Dermoscopy of a skin lesion · imaged for a research study, with no referral diagnosis recorded — 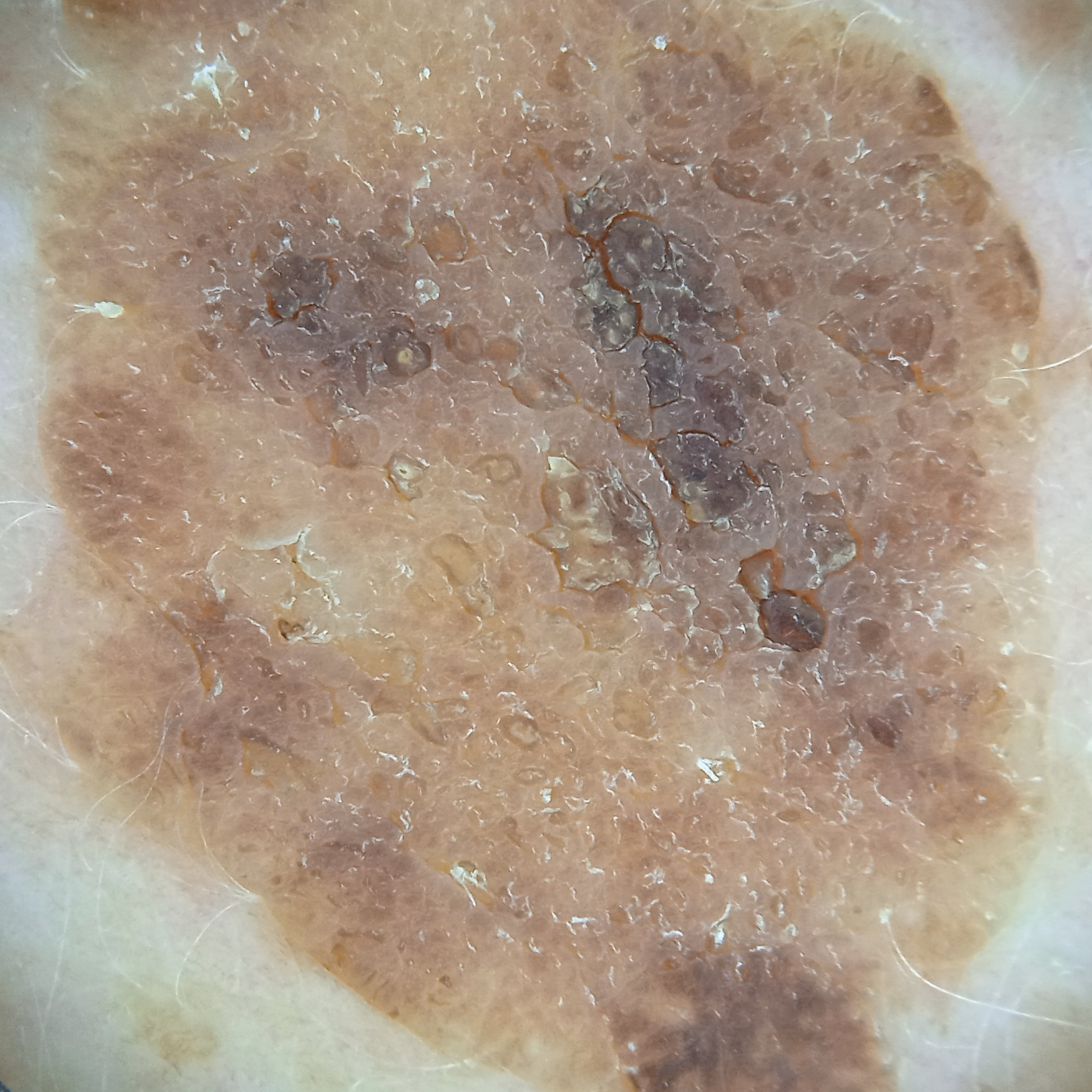anatomic site: the back | size: 15.7 mm | diagnostic label: seborrheic keratosis (dermatologist consensus).